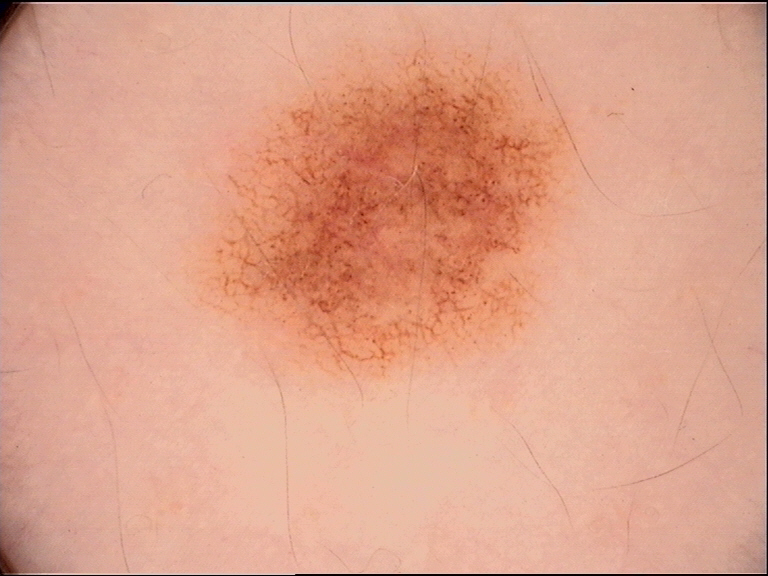The diagnosis was a dysplastic junctional nevus.